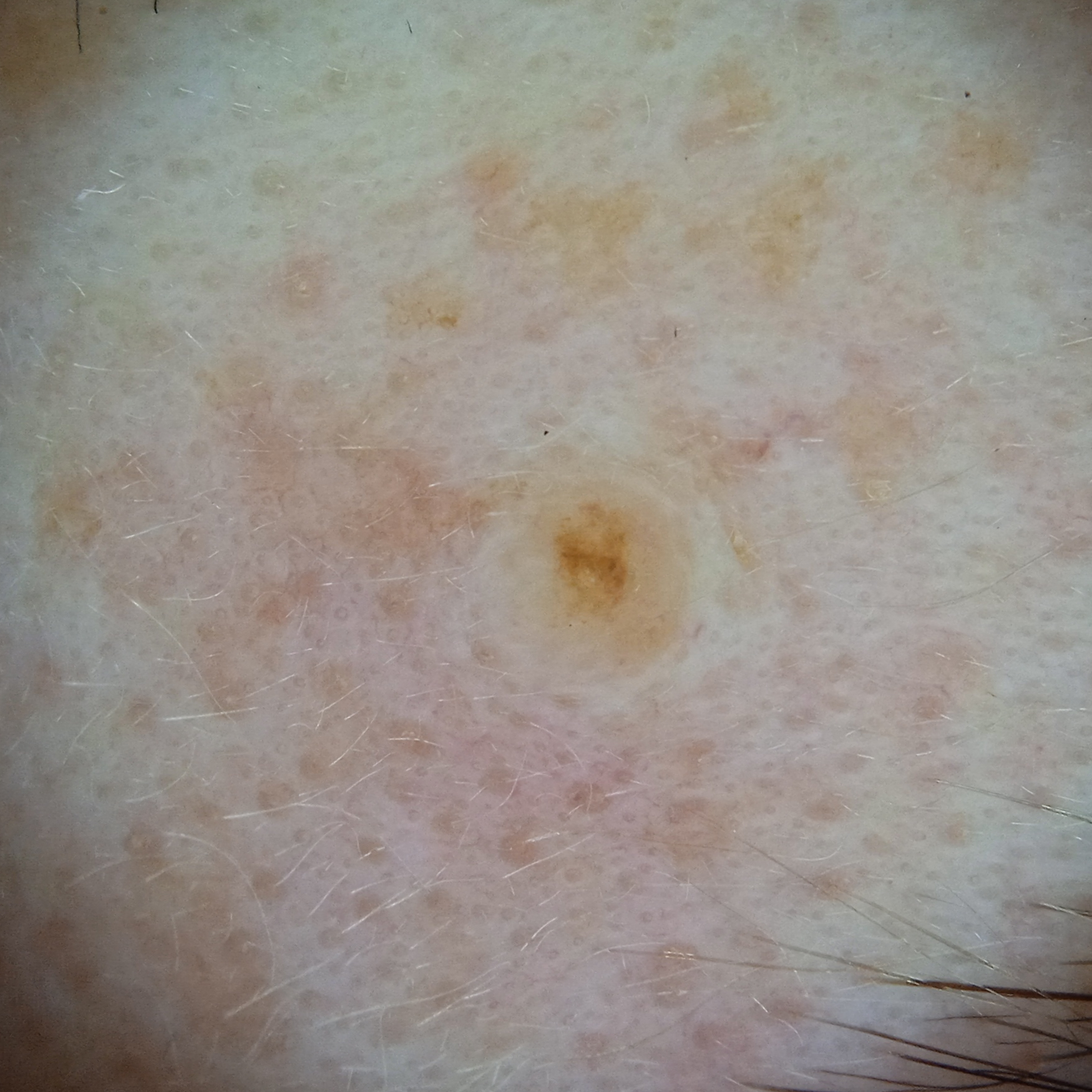Findings:
• referral context: clinical suspicion of melanoma
• subject: female, aged 50
• imaging: dermoscopy
• location: the face
• size: 1.8 mm
• diagnosis: melanocytic nevus (dermatologist consensus)